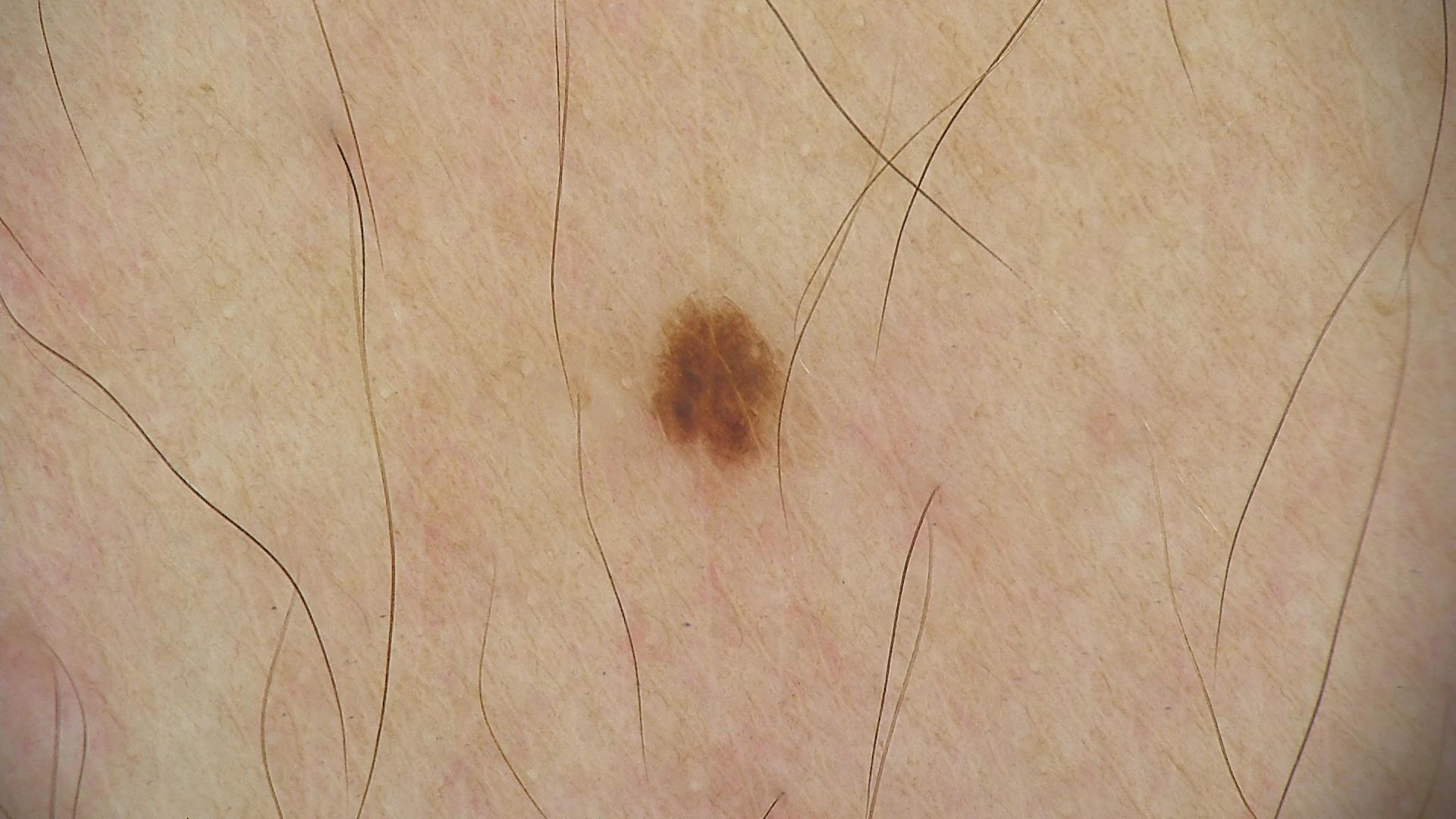A dermatoscopic image of a skin lesion. Labeled as a dysplastic junctional nevus.